A dermatoscopic image of a skin lesion.
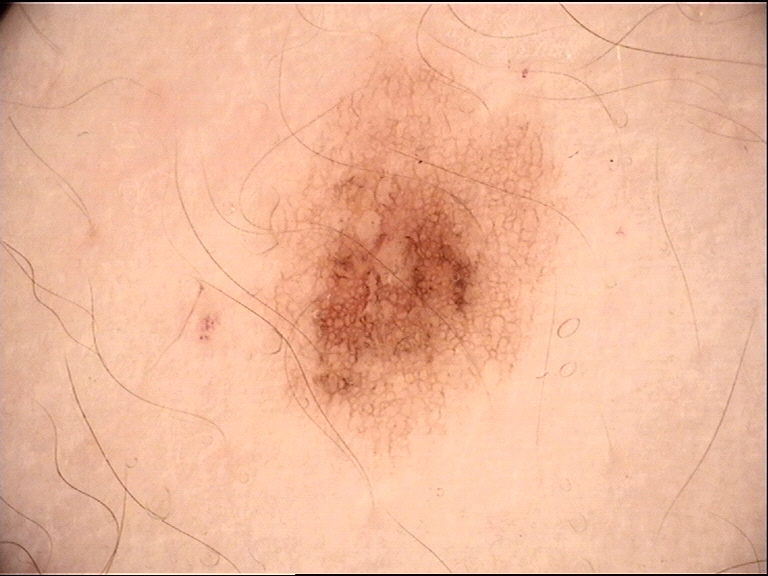  diagnosis:
    name: dysplastic junctional nevus
    code: jd
    malignancy: benign
    super_class: melanocytic
    confirmation: expert consensus